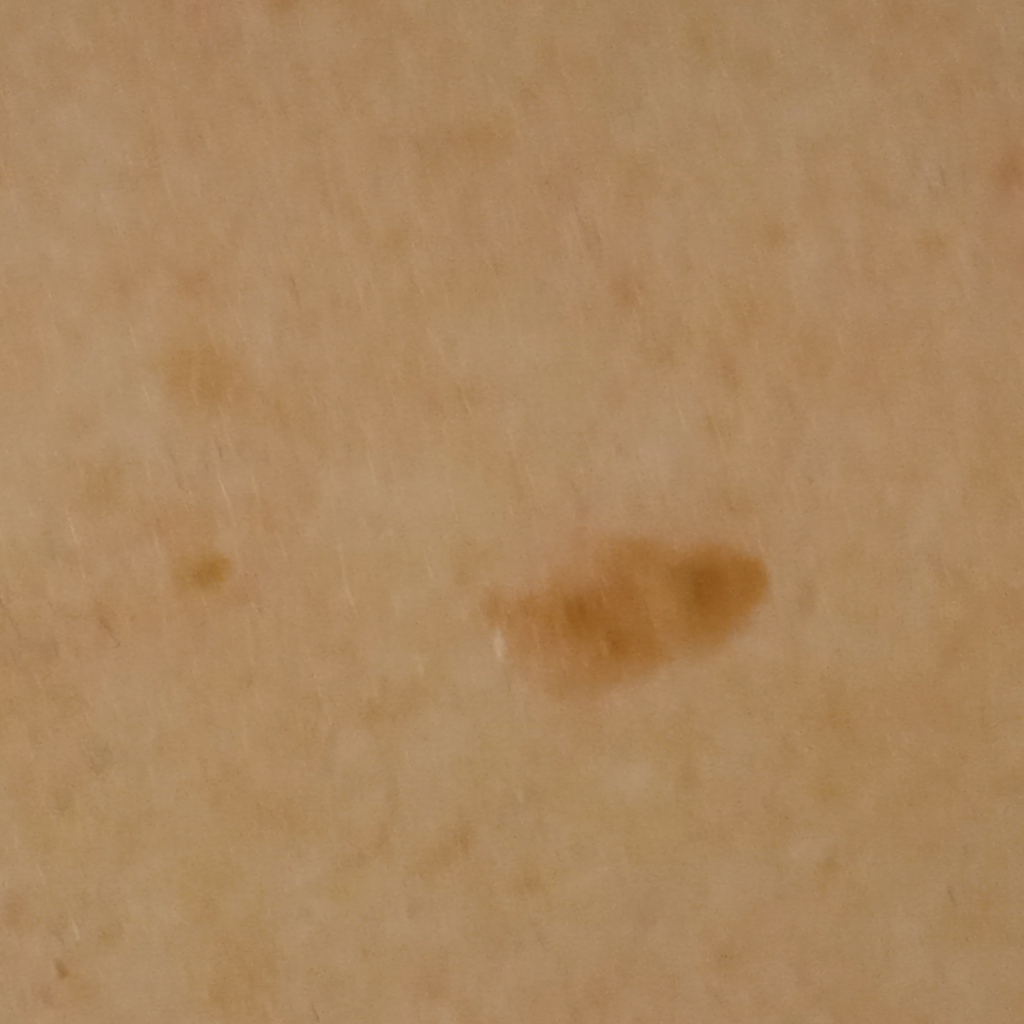<lesion>
<diagnosis>
<name>seborrheic keratosis</name>
<malignancy>benign</malignancy>
</diagnosis>
</lesion>